A close-up photograph. The patient also reports fatigue. The contributor is a male aged 18–29. Texture is reported as flat. No associated lesion symptoms were reported. The patient described the issue as a rash. Present for one to three months. Located on the front of the torso and back of the torso:
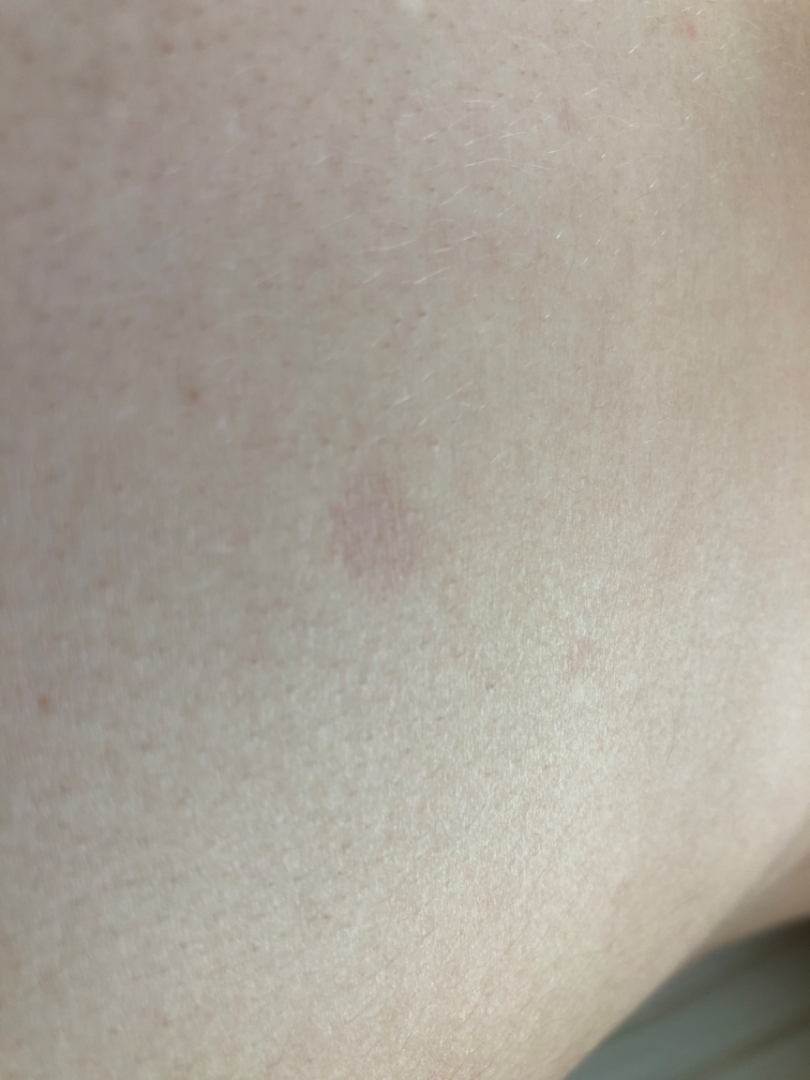The image was not sufficient for the reviewer to characterize the skin condition.